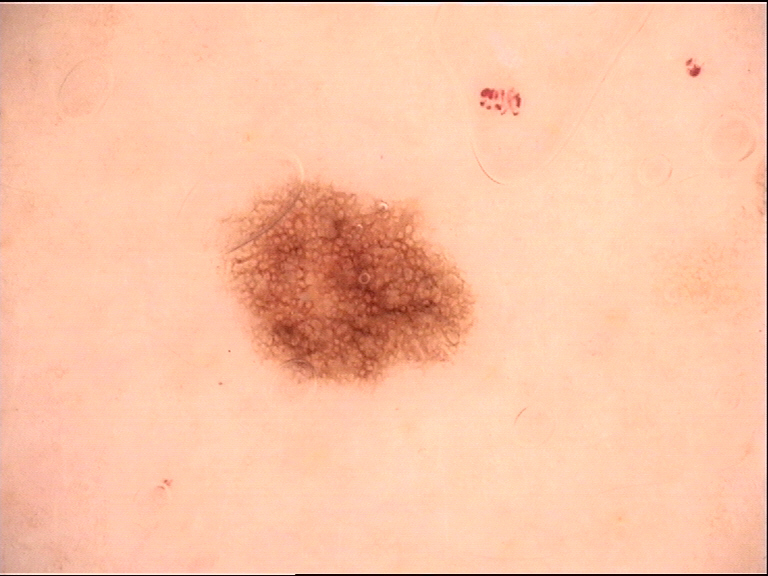A dermoscopy image of a single skin lesion.
The diagnostic label was a benign lesion — a dysplastic junctional nevus.